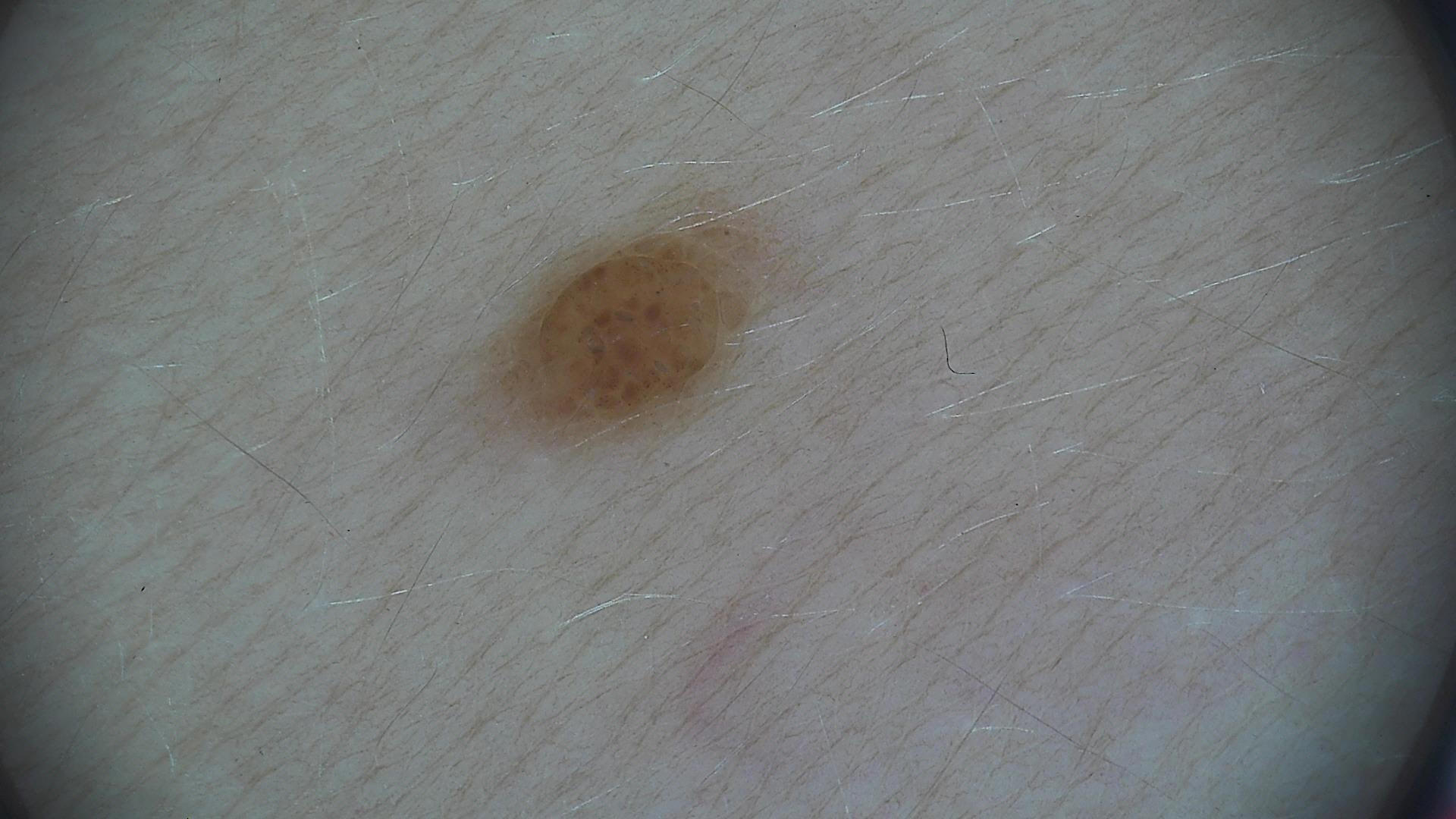| field | value |
|---|---|
| image type | dermatoscopy |
| class | compound nevus (expert consensus) |